The patient is FST II · contact-polarized dermoscopy of a skin lesion · a male patient aged 73 to 77.
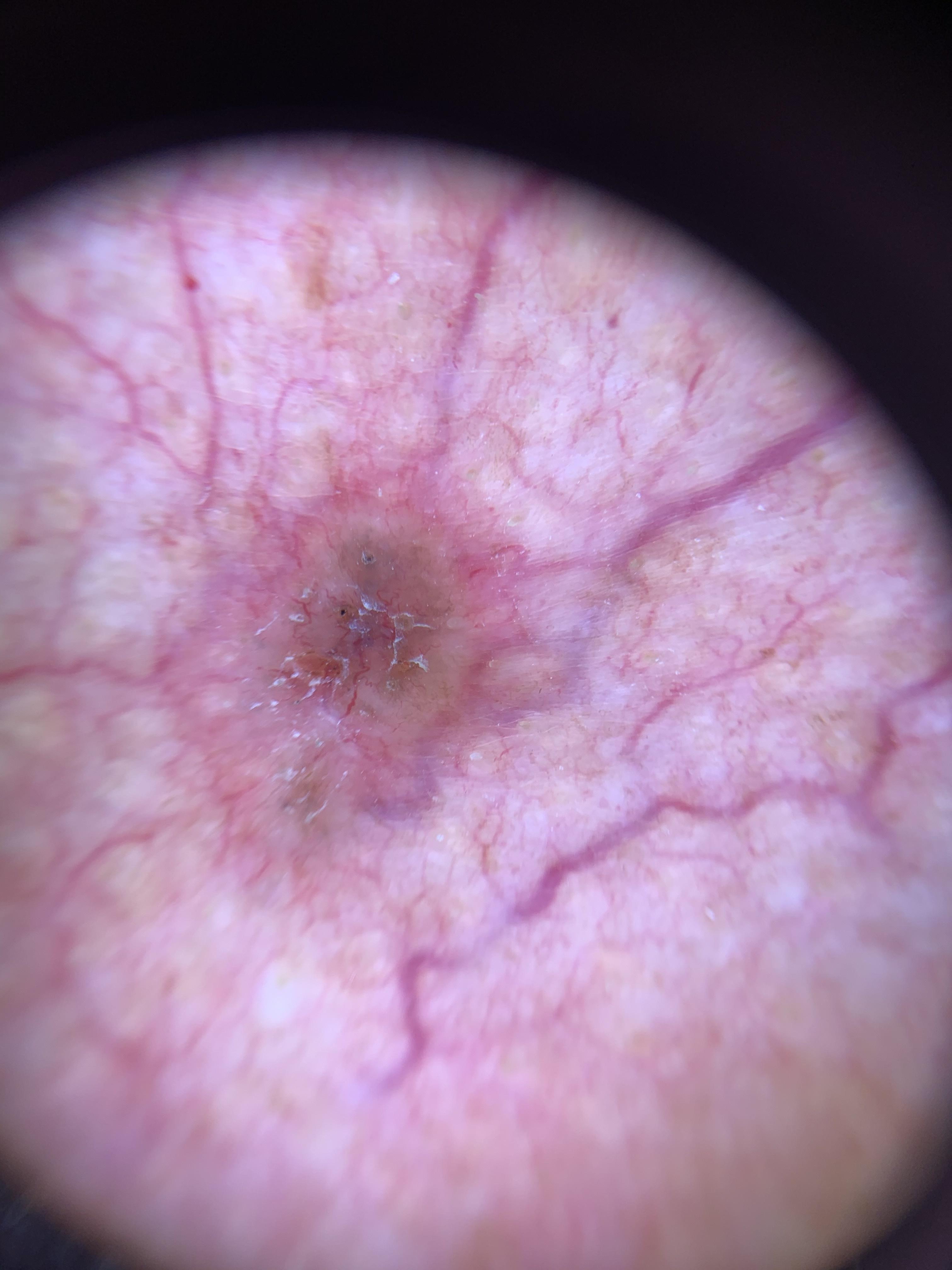Histopathological examination showed a malignant lesion — a basal cell carcinoma.